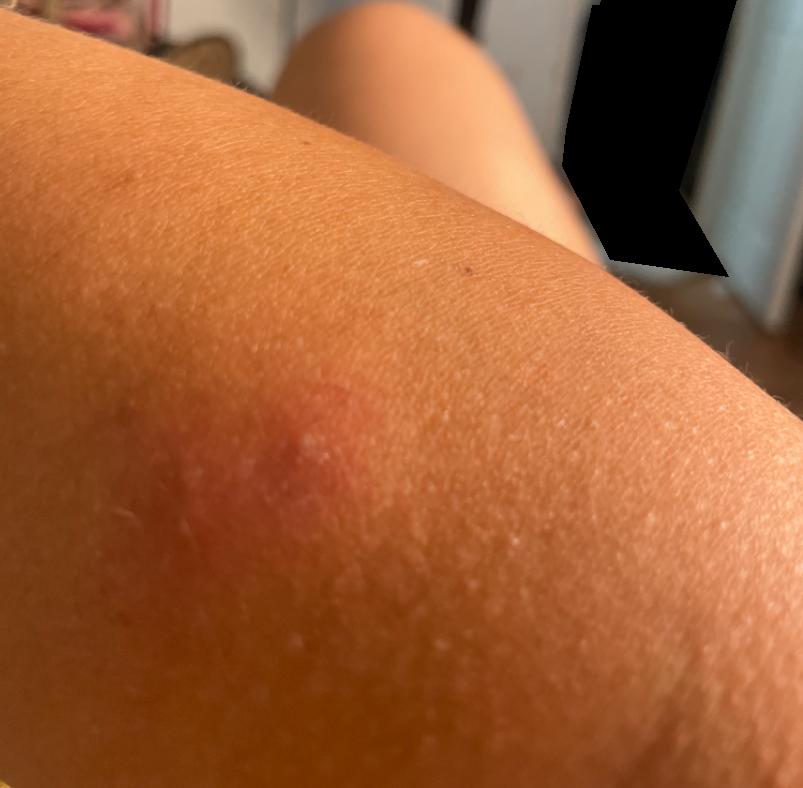Review:
The reviewer was unable to grade this case for skin condition.